A dermoscopic image of a skin lesion:
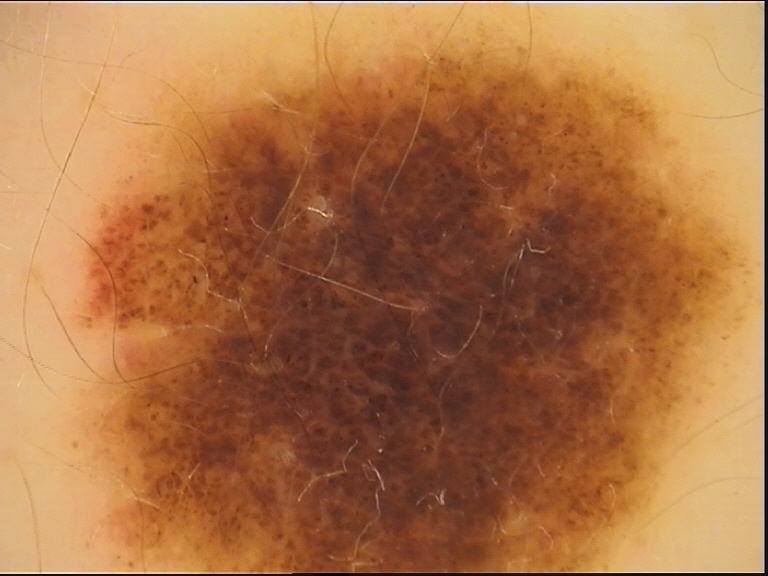category: banal; class: congenital compound nevus (expert consensus).